The photograph was taken at a distance · the back of the torso, head or neck and front of the torso are involved · self-categorized by the patient as skin that appeared healthy to them · the condition has been present for less than one week · Fitzpatrick IV; non-clinician graders estimated Monk skin tone scale 2 or 3 · the lesion is described as rough or flaky and raised or bumpy:
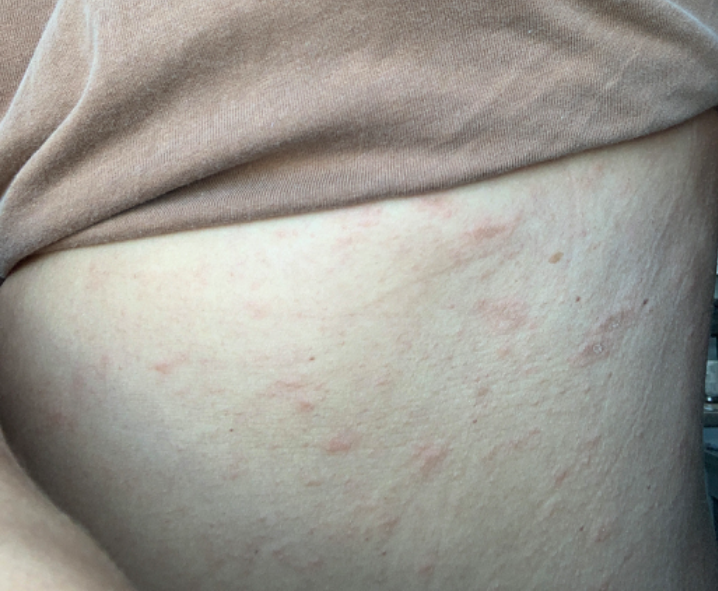<summary>
  <assessment>ungradable on photographic review</assessment>
</summary>